A male patient aged approximately 40. A skin lesion imaged with a dermatoscope — 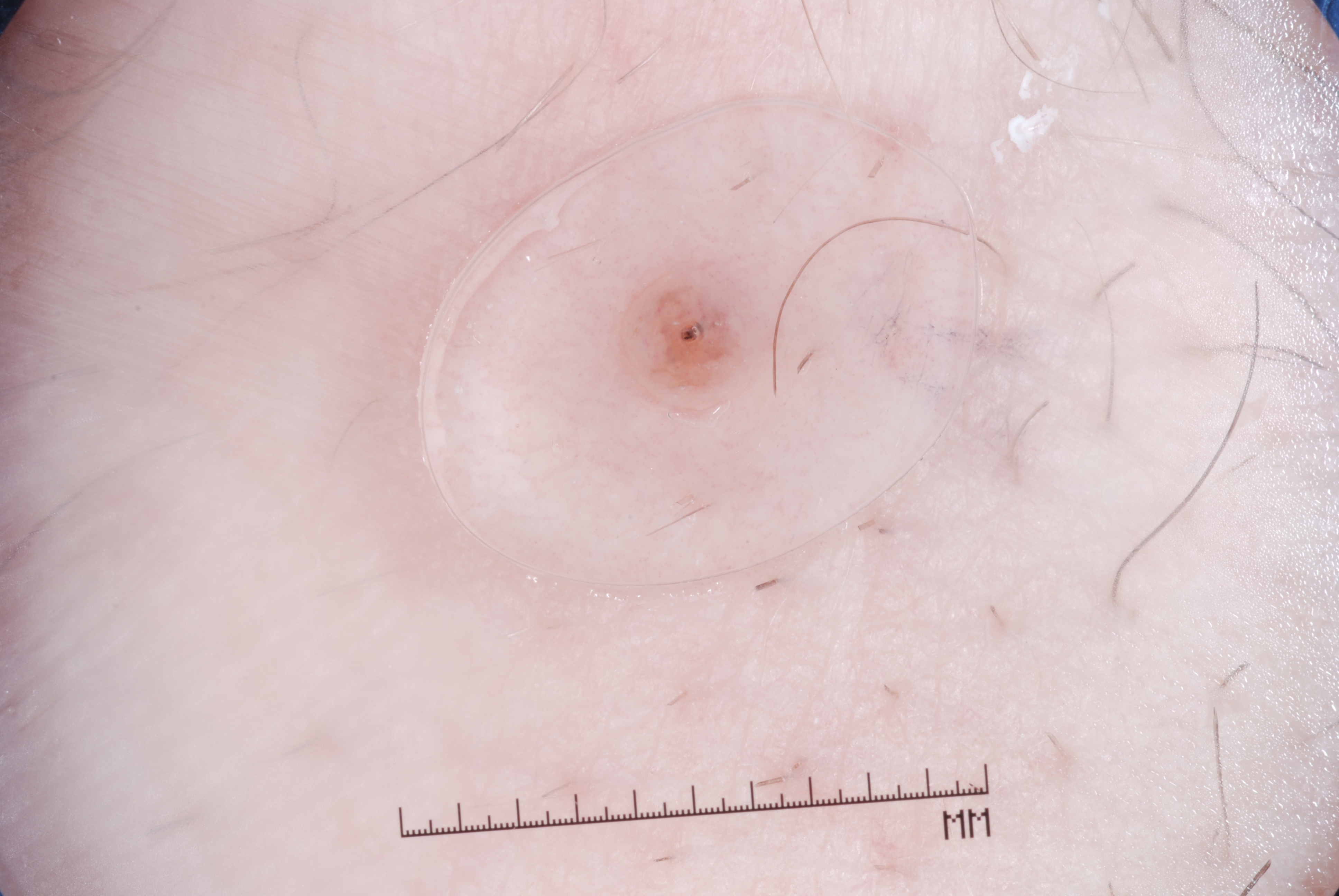Dermoscopic review identifies milia-like cysts.
Lesion location: [619, 257, 761, 415].
Consistent with a melanocytic nevus.